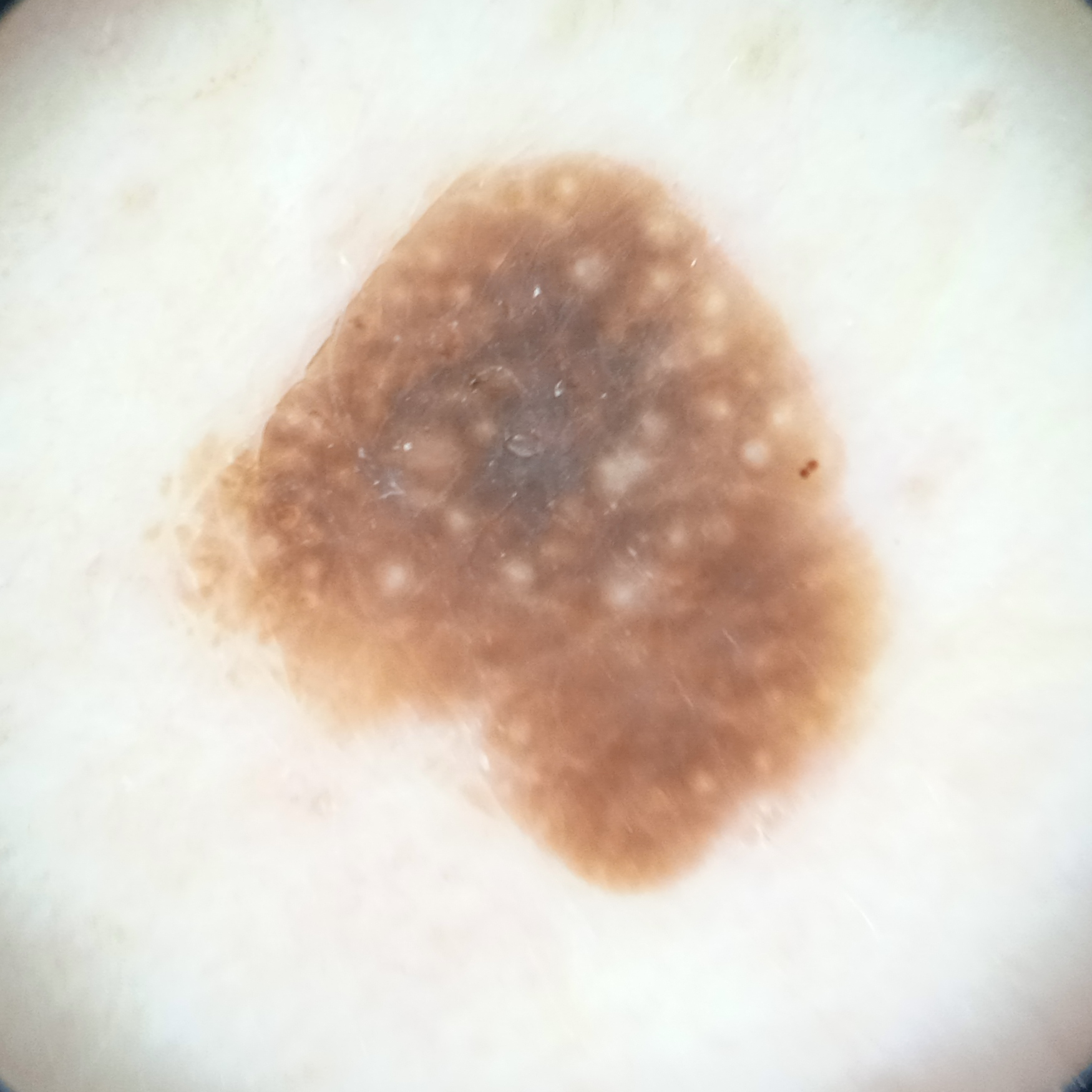Dermoscopy of a skin lesion. The patient says their skin reddens with sun exposure. On a questionnaire the patient reported a personal history of skin cancer, a personal history of cancer, and no immunosuppression. Measuring roughly 8.6 mm. The dermatologists' assessment was a seborrheic keratosis.